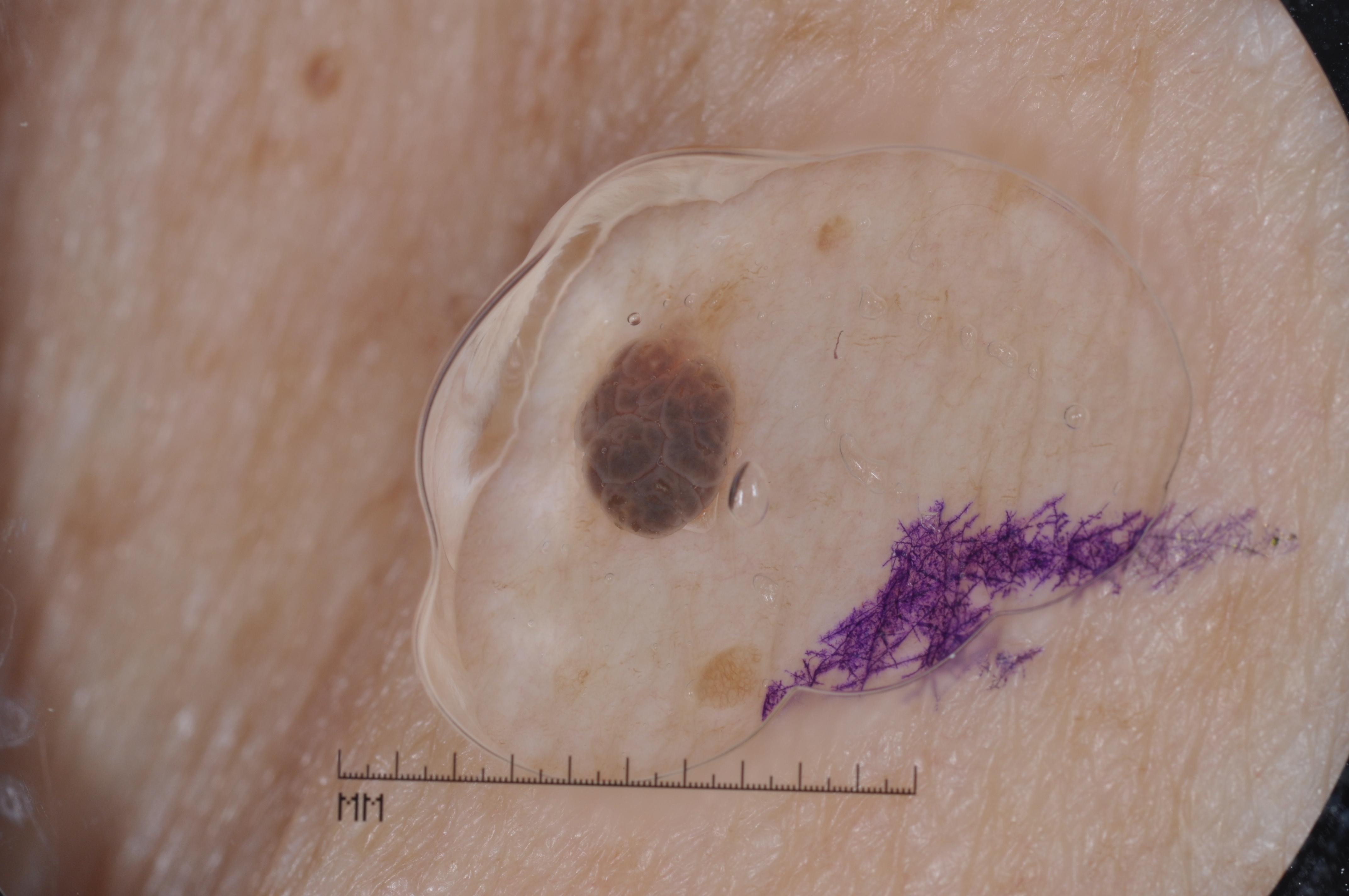Image and clinical context: A dermoscopic view of a skin lesion. The lesion is located at [574, 322, 740, 539]. Conclusion: The lesion was assessed as a seborrheic keratosis.